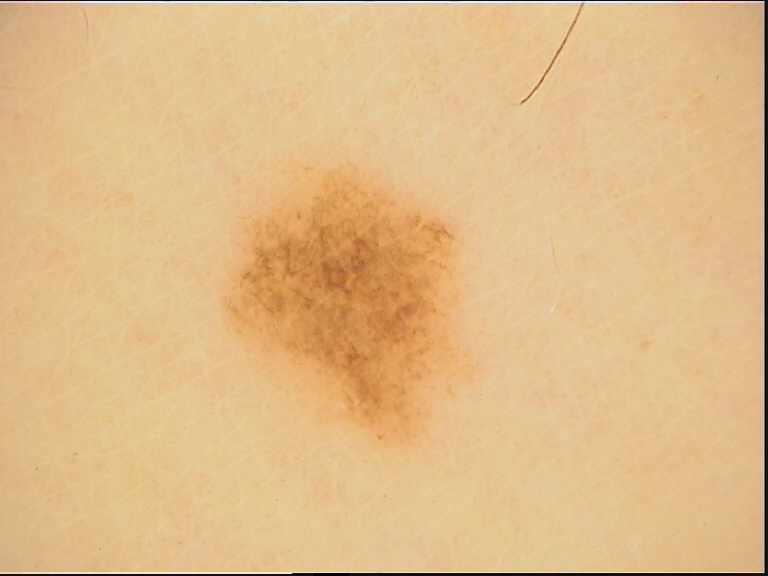Conclusion:
The diagnostic label was a dysplastic junctional nevus.